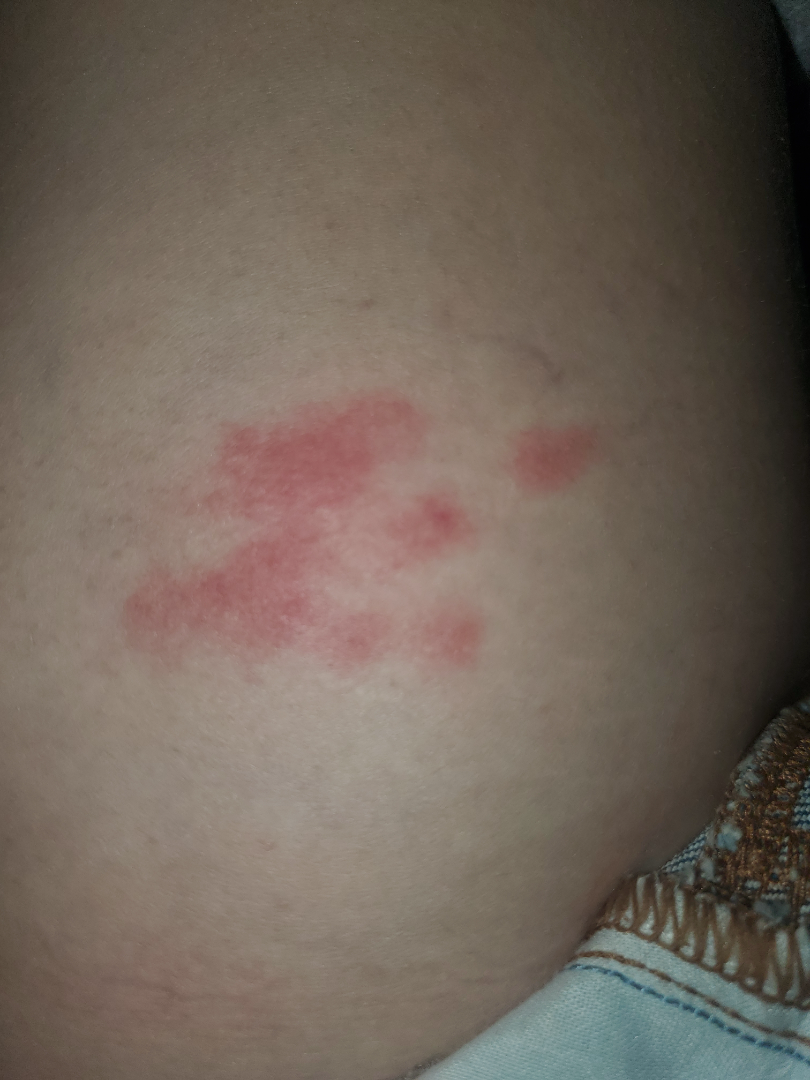Findings:
• image framing · close-up
• differential · most likely Herpes Zoster; with consideration of Acute dermatitis, NOS